A macroscopic clinical photograph of a skin lesion; a female patient 32 years of age: 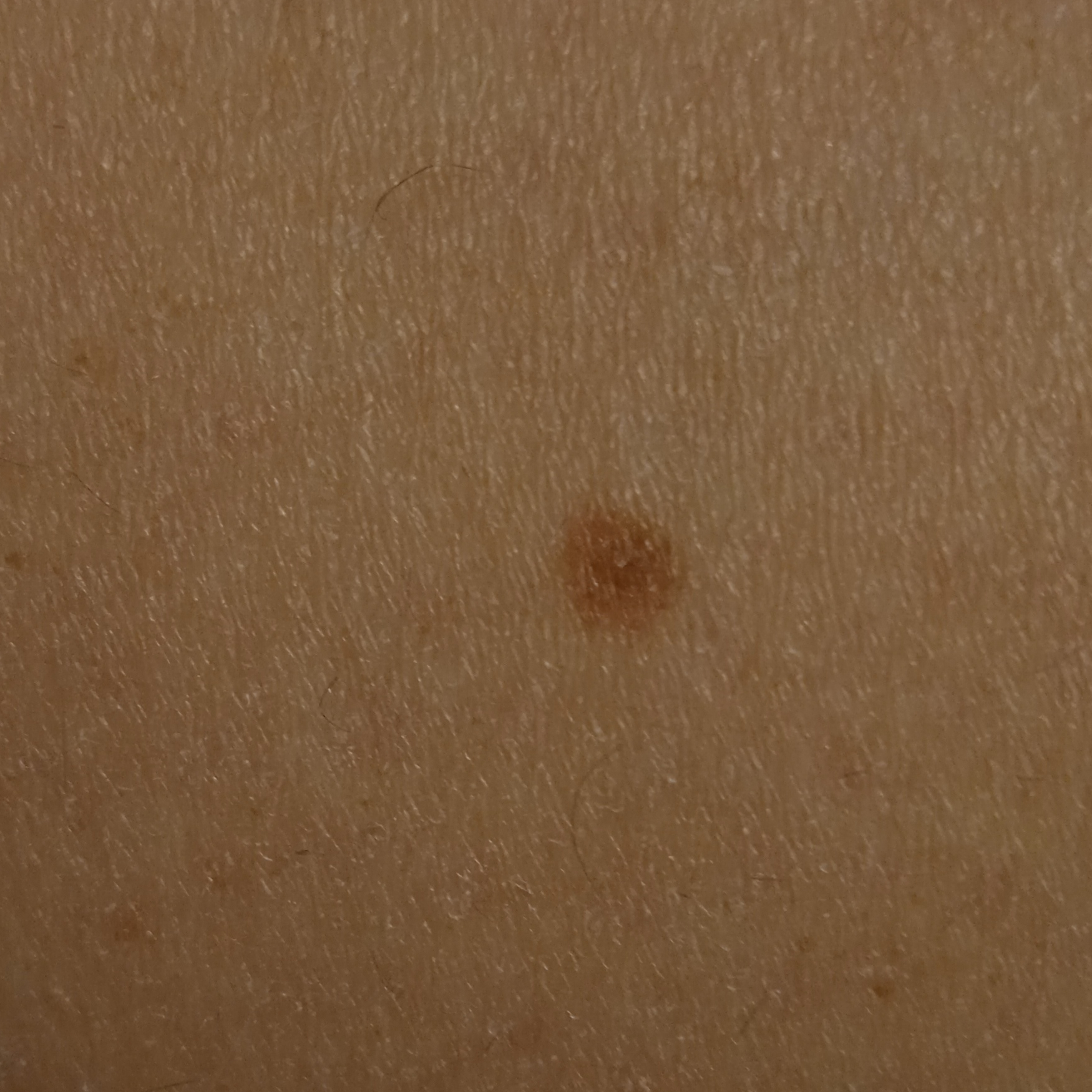Located on a leg. The lesion is about 4.1 mm across. The consensus diagnosis for this lesion was a melanocytic nevus.